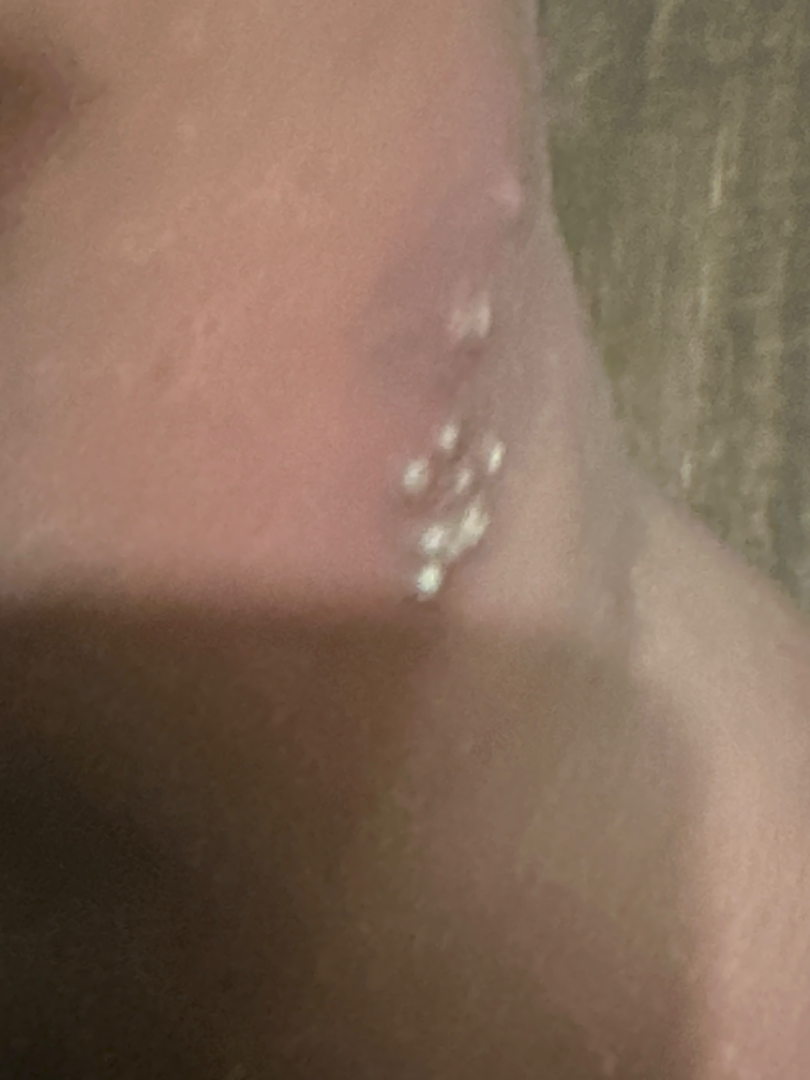History:
The photograph is a close-up of the affected area. FST V.
Impression:
On photographic review by a dermatologist: in keeping with Milia.